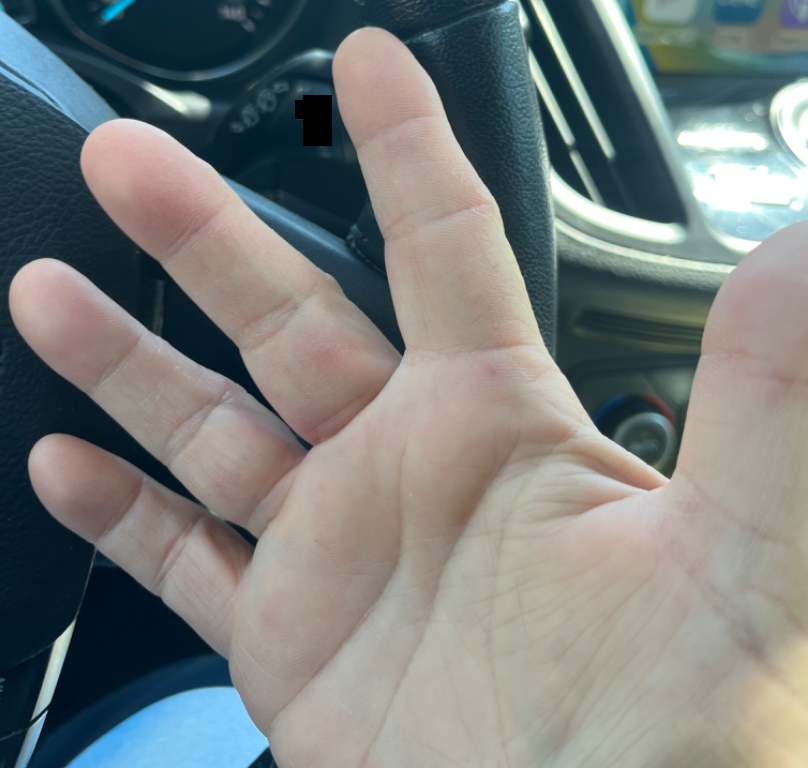Assessment:
The case was indeterminate on photographic review.
Clinical context:
The photograph was taken at a distance. Reported duration is about one day. The subject is 50–59, female. Symptoms reported: pain. Texture is reported as raised or bumpy. The palm is involved. Self-categorized by the patient as skin that appeared healthy to them. The patient indicates associated fatigue.